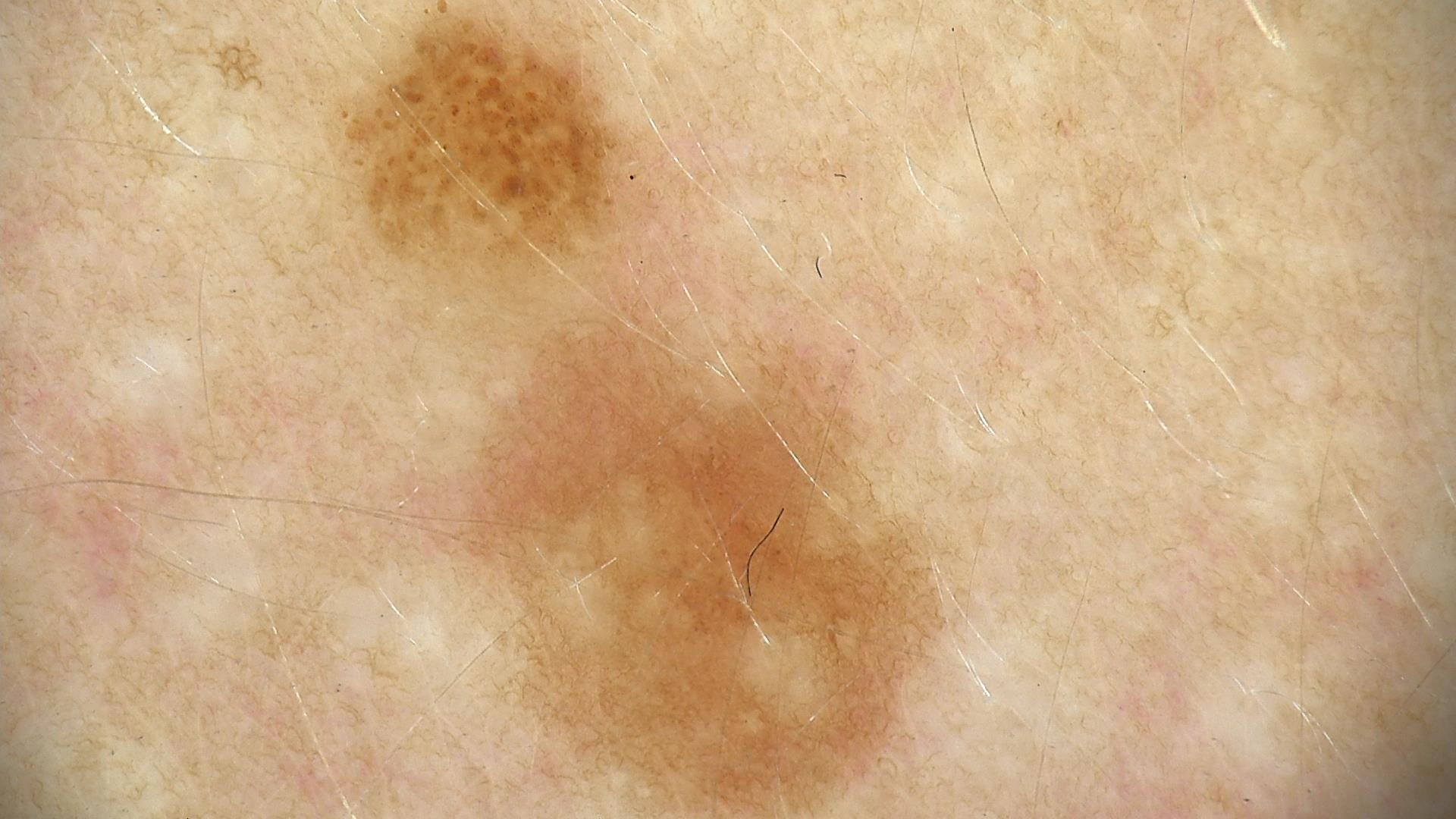Impression:
The diagnosis was a dysplastic junctional nevus.